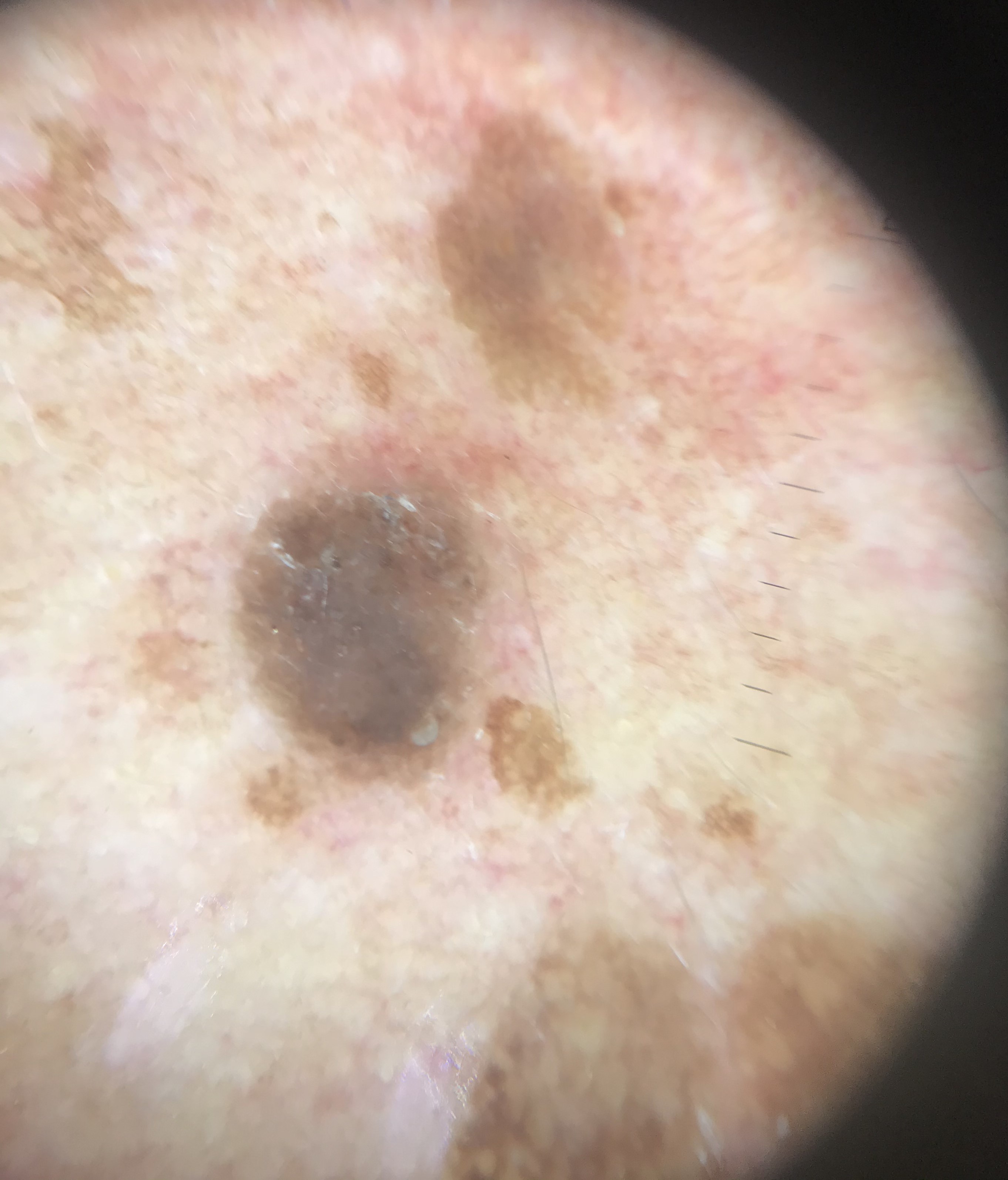A skin lesion imaged with a dermatoscope. The architecture is that of a keratinocytic lesion. The diagnostic label was a benign lesion — a seborrheic keratosis.